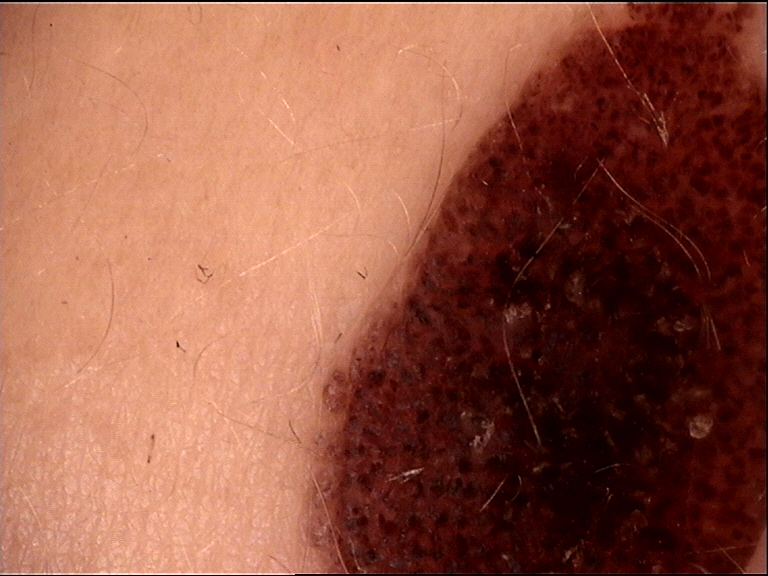A dermoscopic close-up of a skin lesion. Diagnosed as a banal lesion — a congenital compound nevus.